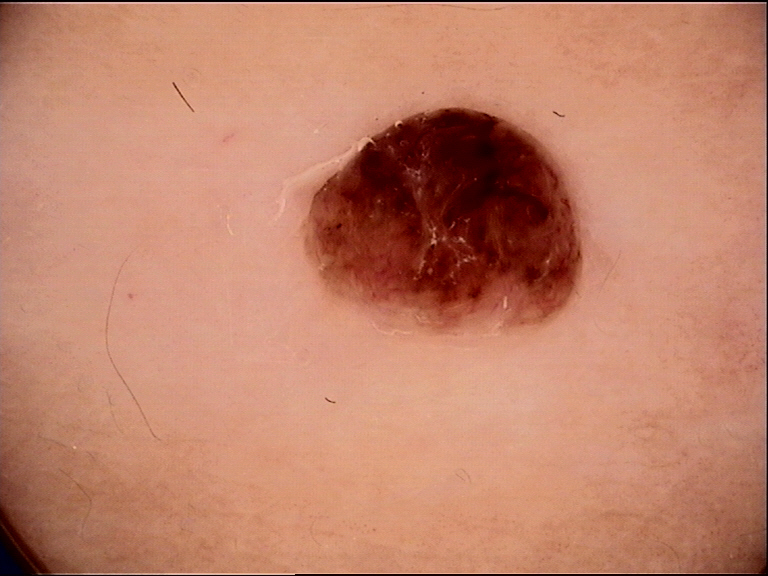Case:
• diagnosis · dermal nevus (expert consensus)